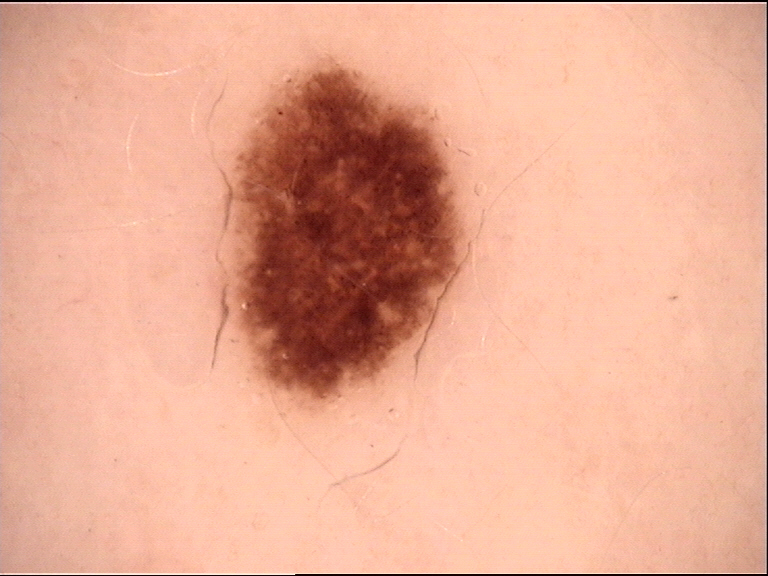A dermatoscopic image of a skin lesion. Classified as a dysplastic junctional nevus.